A dermatoscopic image of a skin lesion.
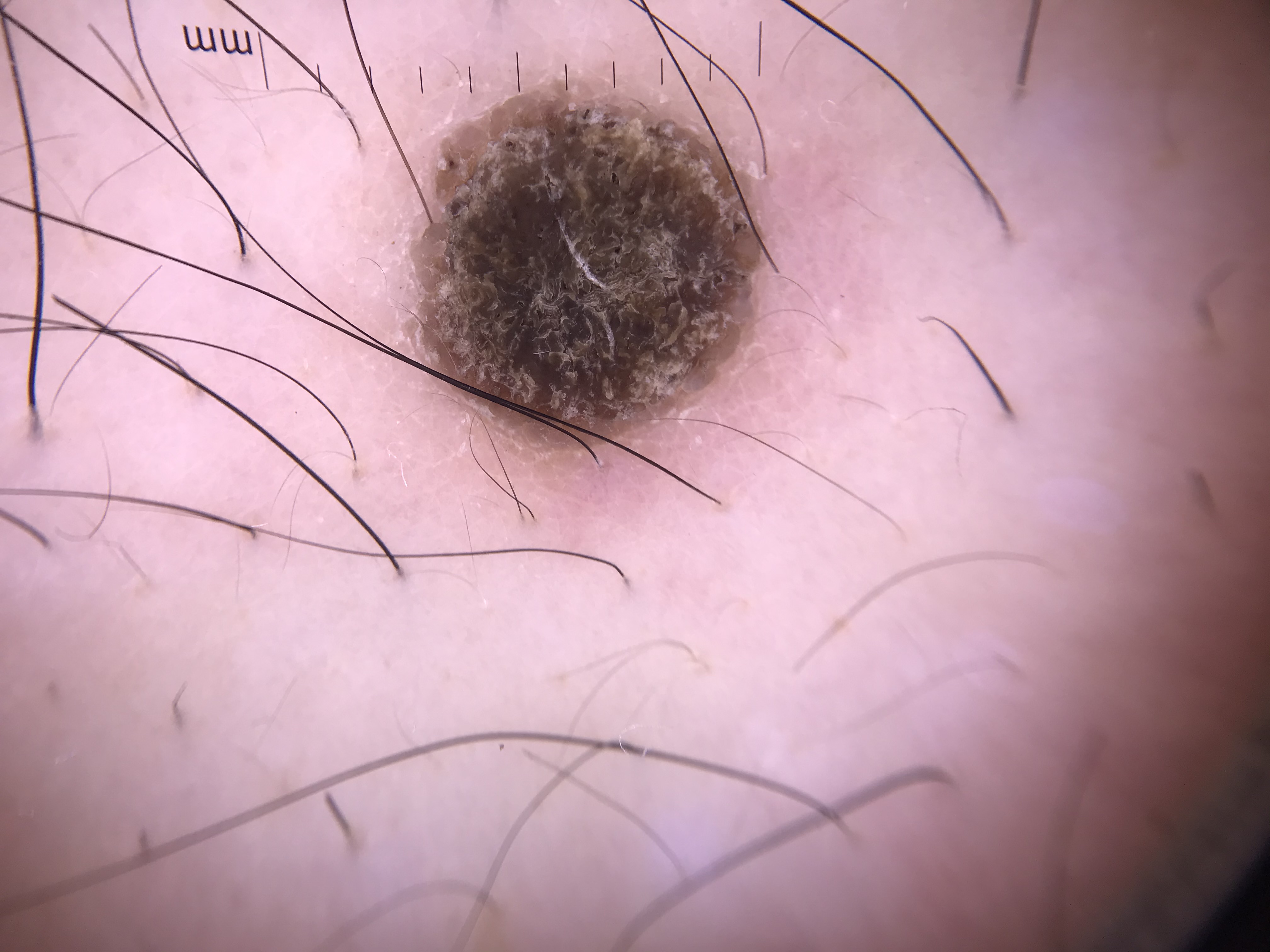assessment = seborrheic keratosis (expert consensus).